A dermoscopy image of a single skin lesion. A male patient aged 68-72:
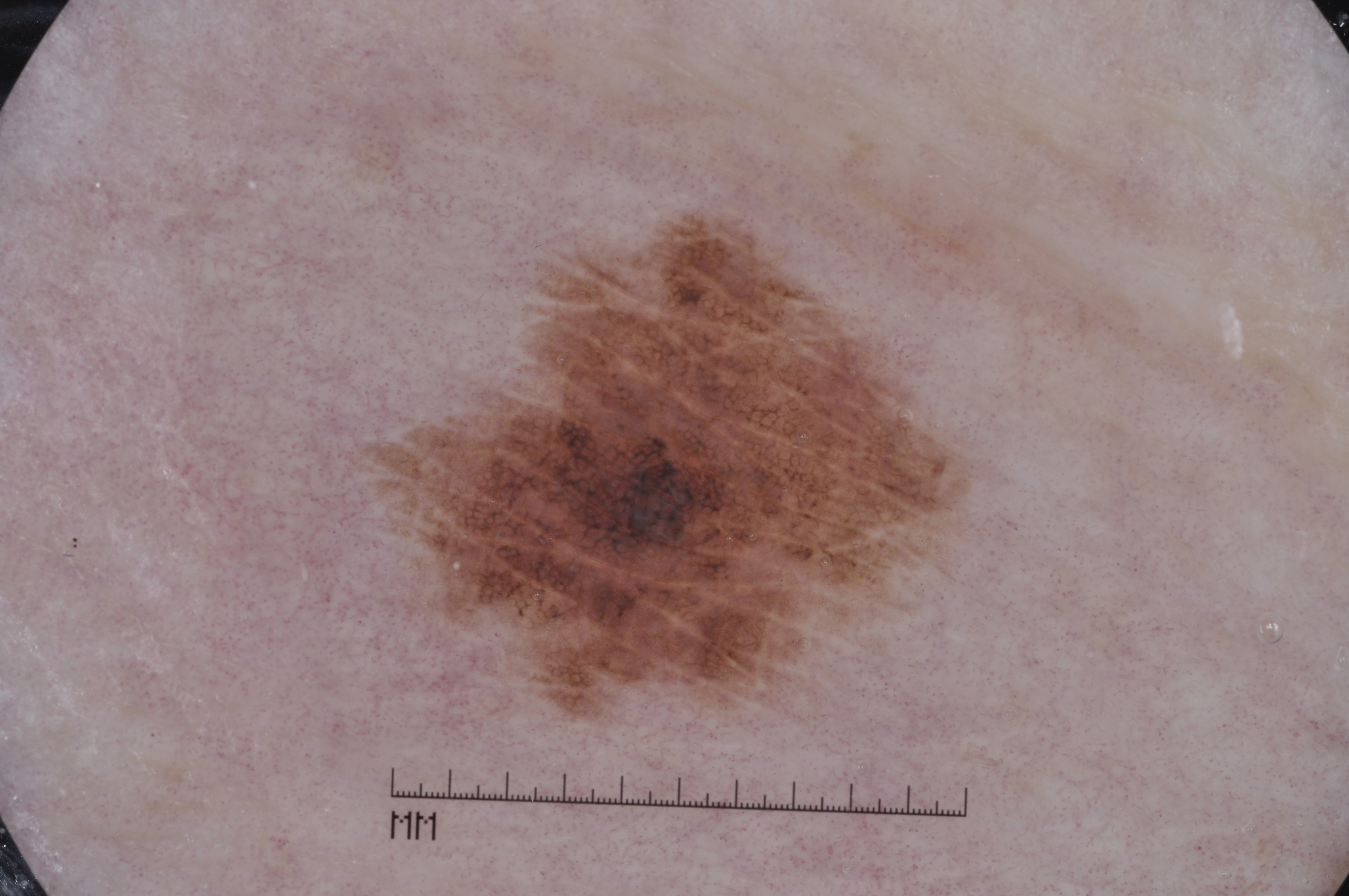{
  "dermoscopic_features": {
    "present": [
      "milia-like cysts",
      "pigment network"
    ],
    "absent": [
      "streaks",
      "negative network"
    ]
  },
  "lesion_location": {
    "bbox_xyxy": [
      359,
      208,
      972,
      726
    ]
  },
  "lesion_extent": "moderate",
  "diagnosis": {
    "name": "melanoma",
    "malignancy": "malignant",
    "lineage": "melanocytic",
    "provenance": "histopathology"
  }
}